The photograph was taken at an angle, the back of the torso is involved:
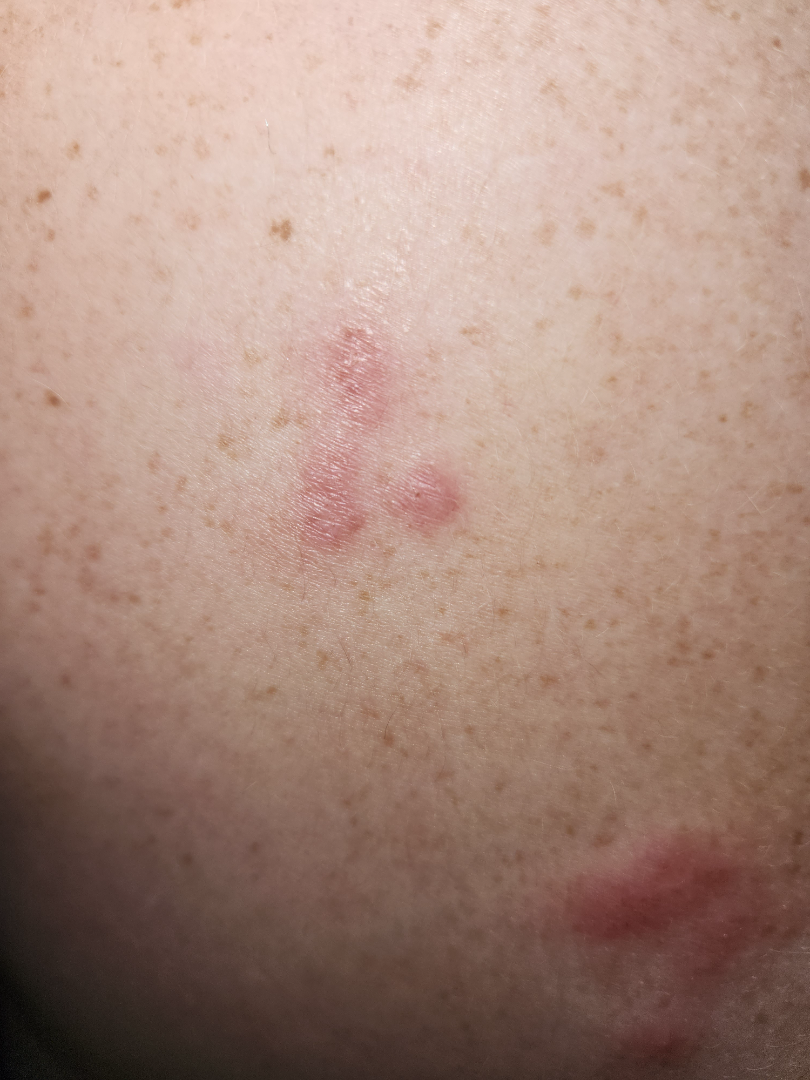The case was difficult to assess from the available photograph.